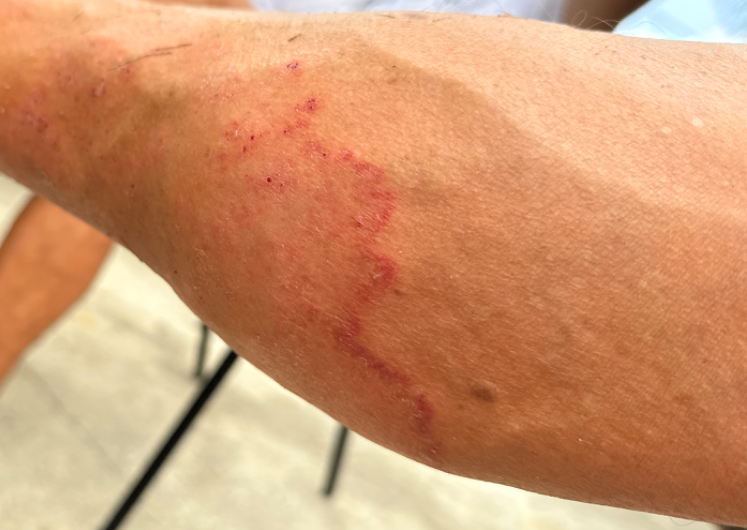The affected area is the leg. The lesion is described as raised or bumpy. This is a close-up image. The condition has been present for one to four weeks. Most consistent with Tinea; with consideration of Stasis Dermatitis; possibly Eczema.